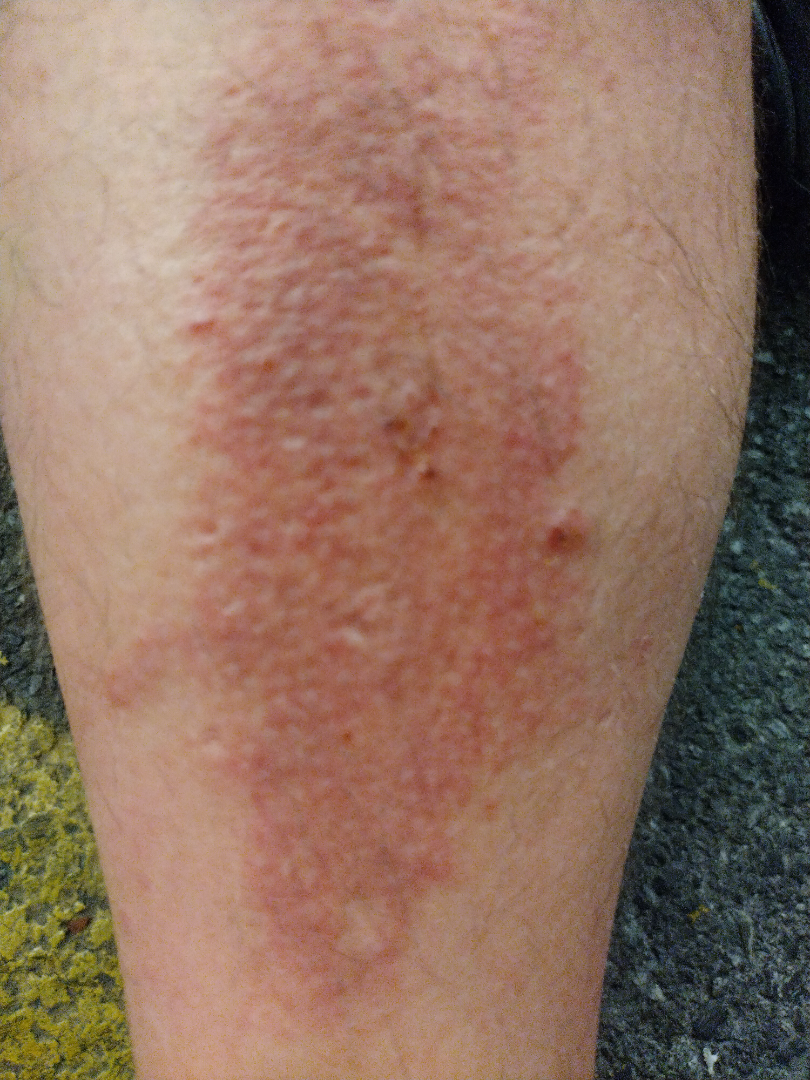This is a close-up image. The lesion involves the leg. The patient is a male aged 30–39. On photographic review by a dermatologist, Allergic Contact Dermatitis (primary); Eczema (considered); Amyloidosis of skin (considered).